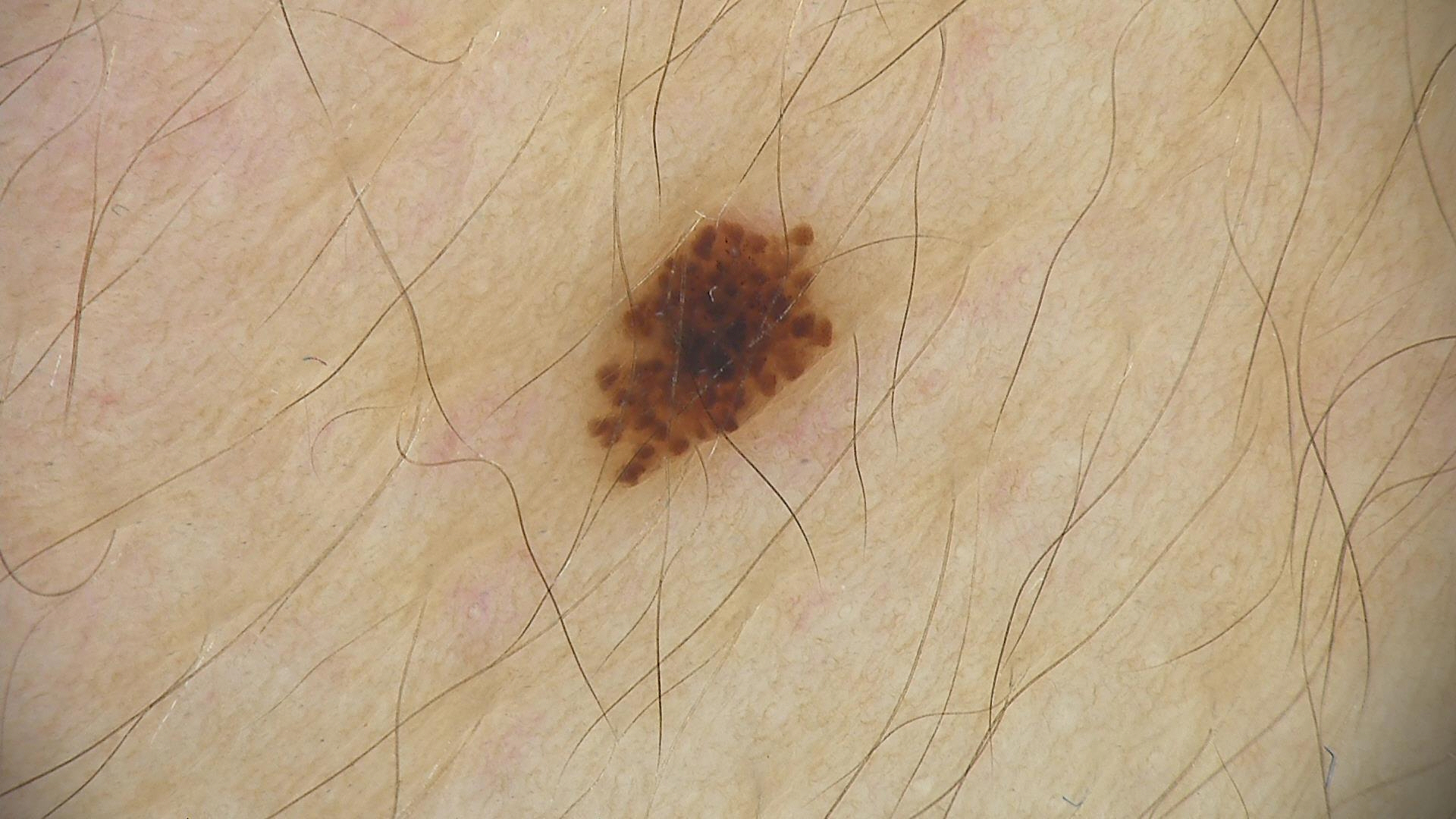• assessment — dysplastic junctional nevus (expert consensus)